A male patient aged 53 to 57. A dermoscopic image of a skin lesion.
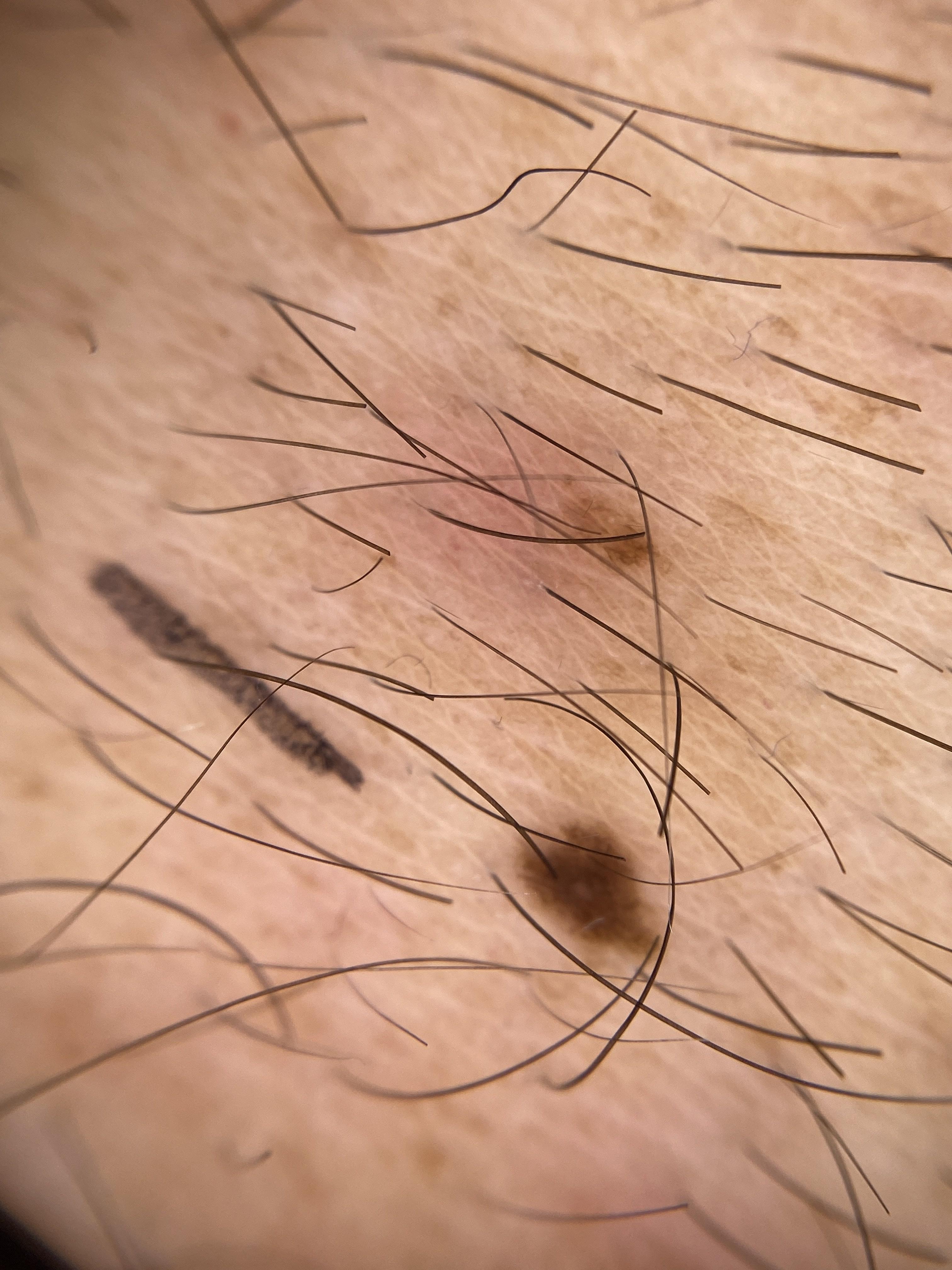Case summary: The lesion was found on the trunk. Conclusion: Histopathology confirmed a nevus.